The contributor is a female aged 40–49. An image taken at a distance. The affected area is the arm.
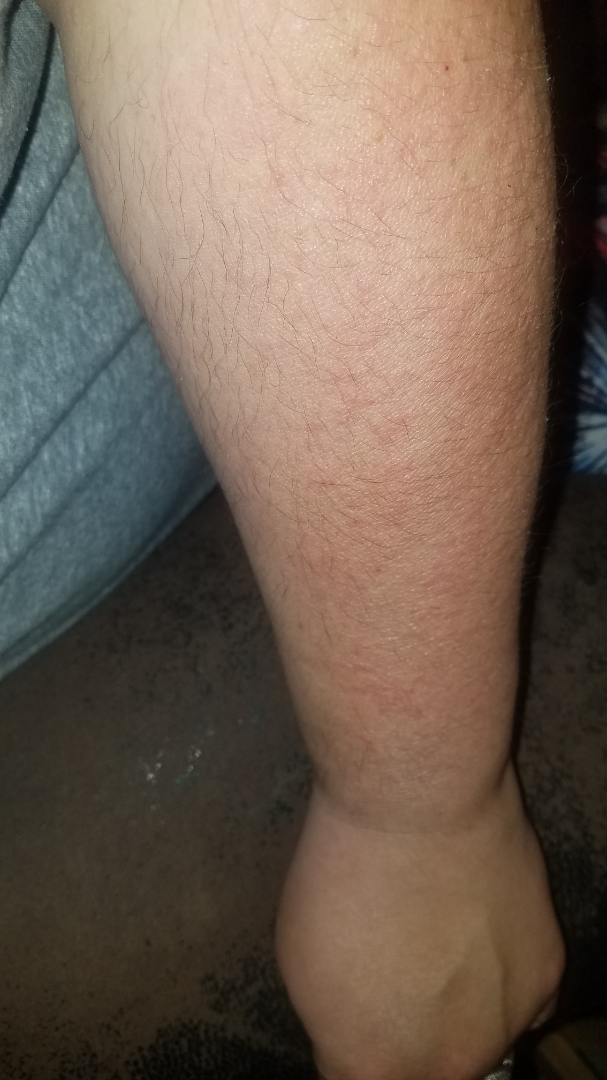{
  "assessment": "ungradable on photographic review",
  "texture": "raised or bumpy",
  "symptoms": [
    "itching",
    "burning"
  ],
  "systemic_symptoms": "none reported",
  "patient_category": "a rash"
}